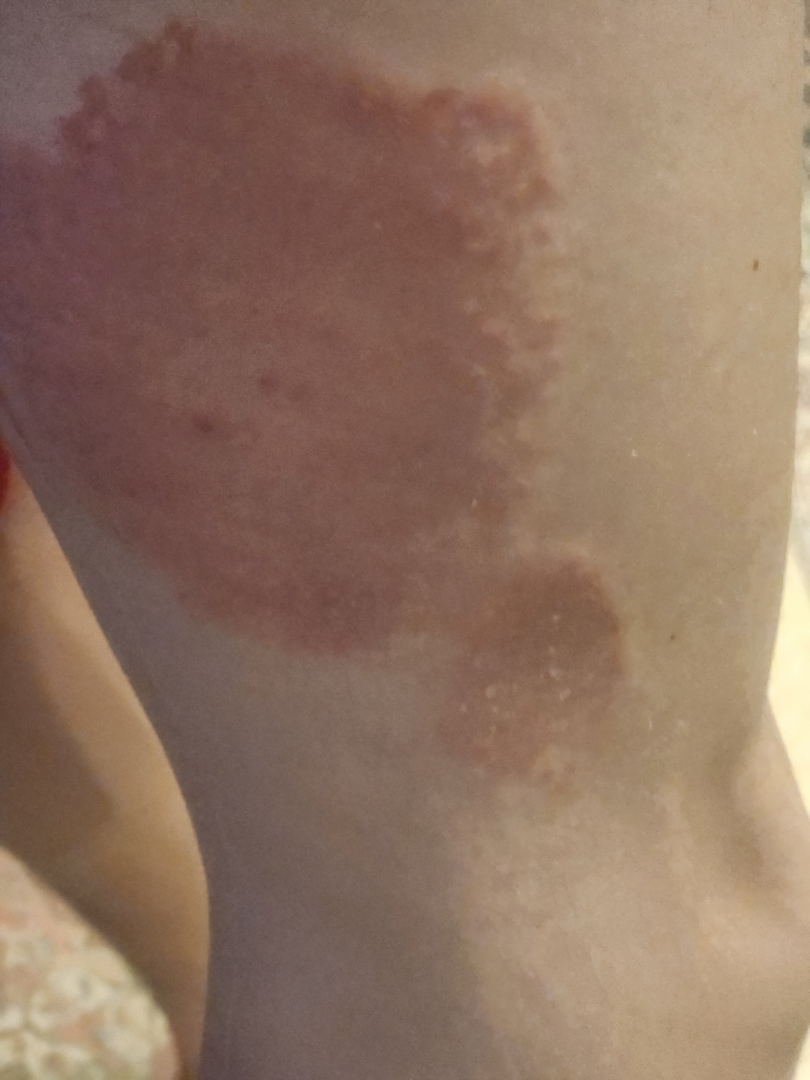Clinical context: A close-up photograph. Assessment: The reviewing dermatologist's impression was: the leading consideration is Psoriasis; also on the differential is Eczema.